Dermoscopy of a skin lesion.
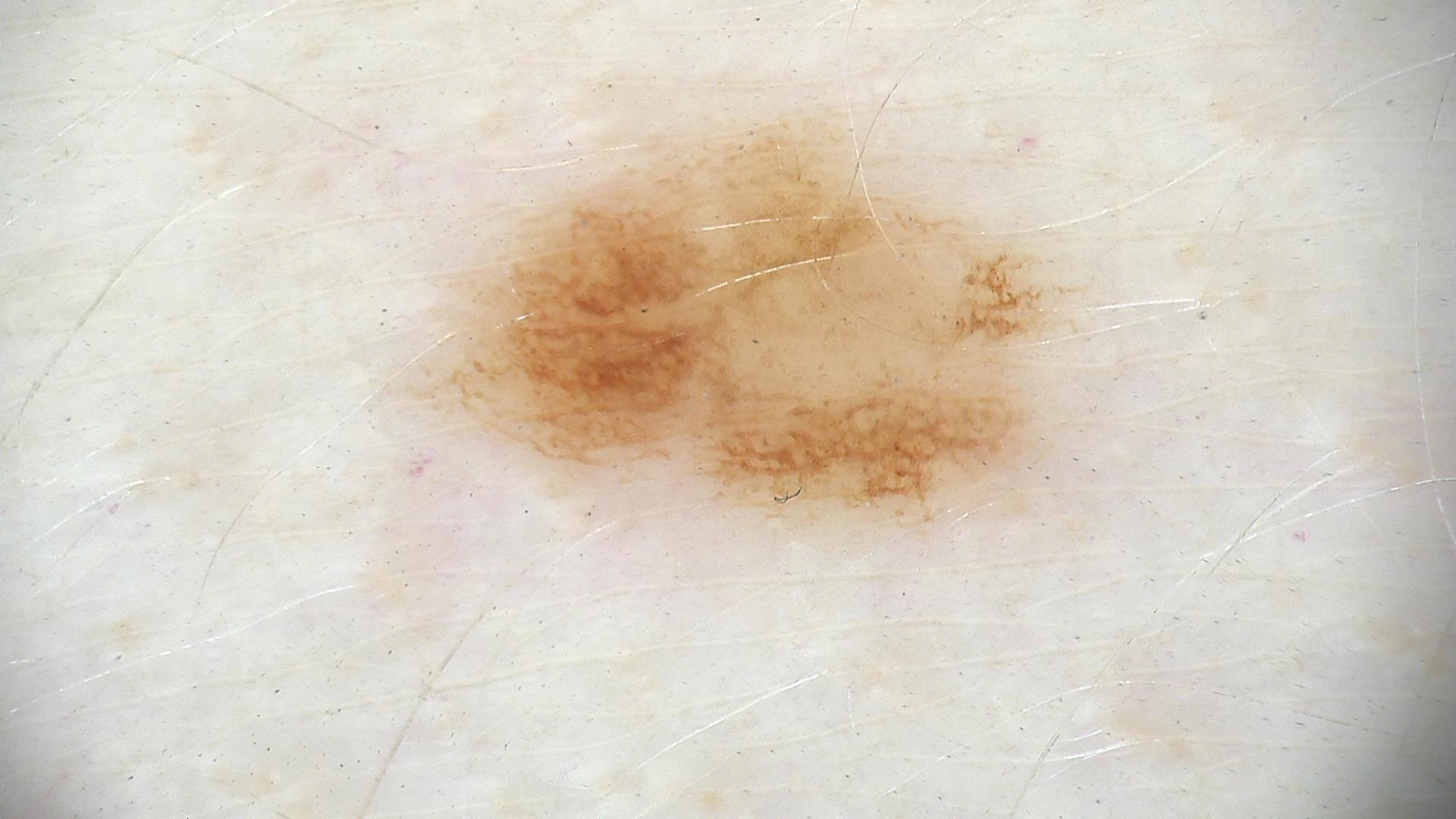diagnosis: dysplastic junctional nevus (expert consensus).